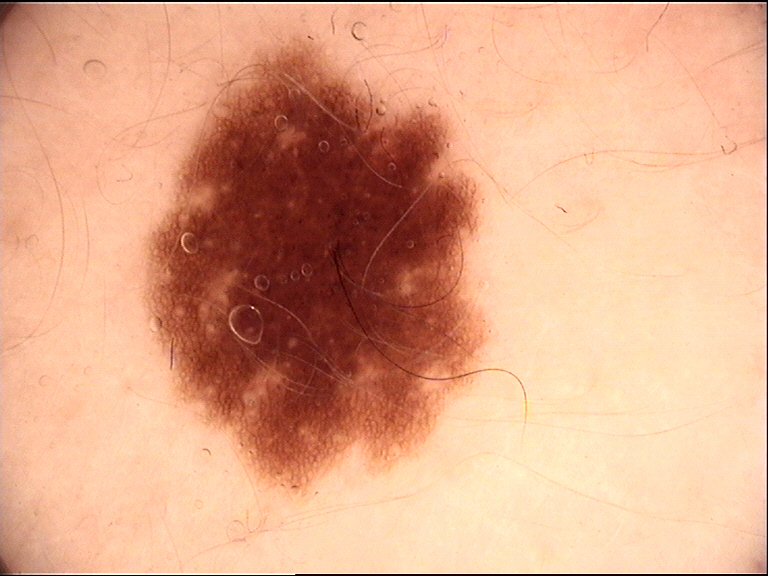Conclusion: The diagnosis was a dysplastic junctional nevus.